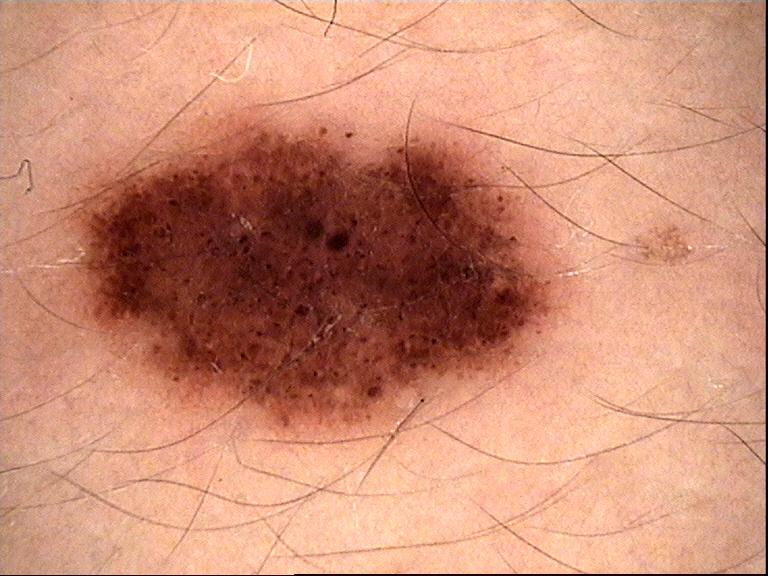Findings:
• diagnosis: dysplastic junctional nevus (expert consensus)